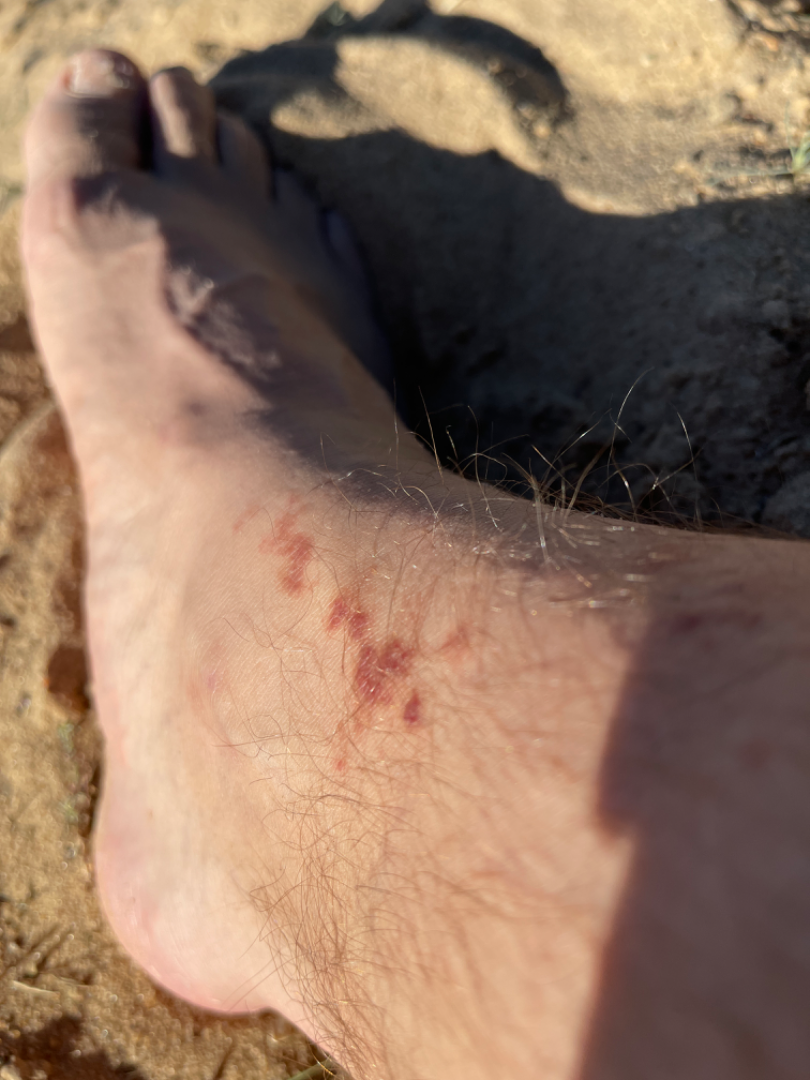| feature | finding |
|---|---|
| clinical impression | the differential includes Lichen planus/lichenoid eruption, Pigmented purpuric eruption and Kaposi's sarcoma of skin, with no clear leading consideration |